A skin lesion imaged with a dermatoscope.
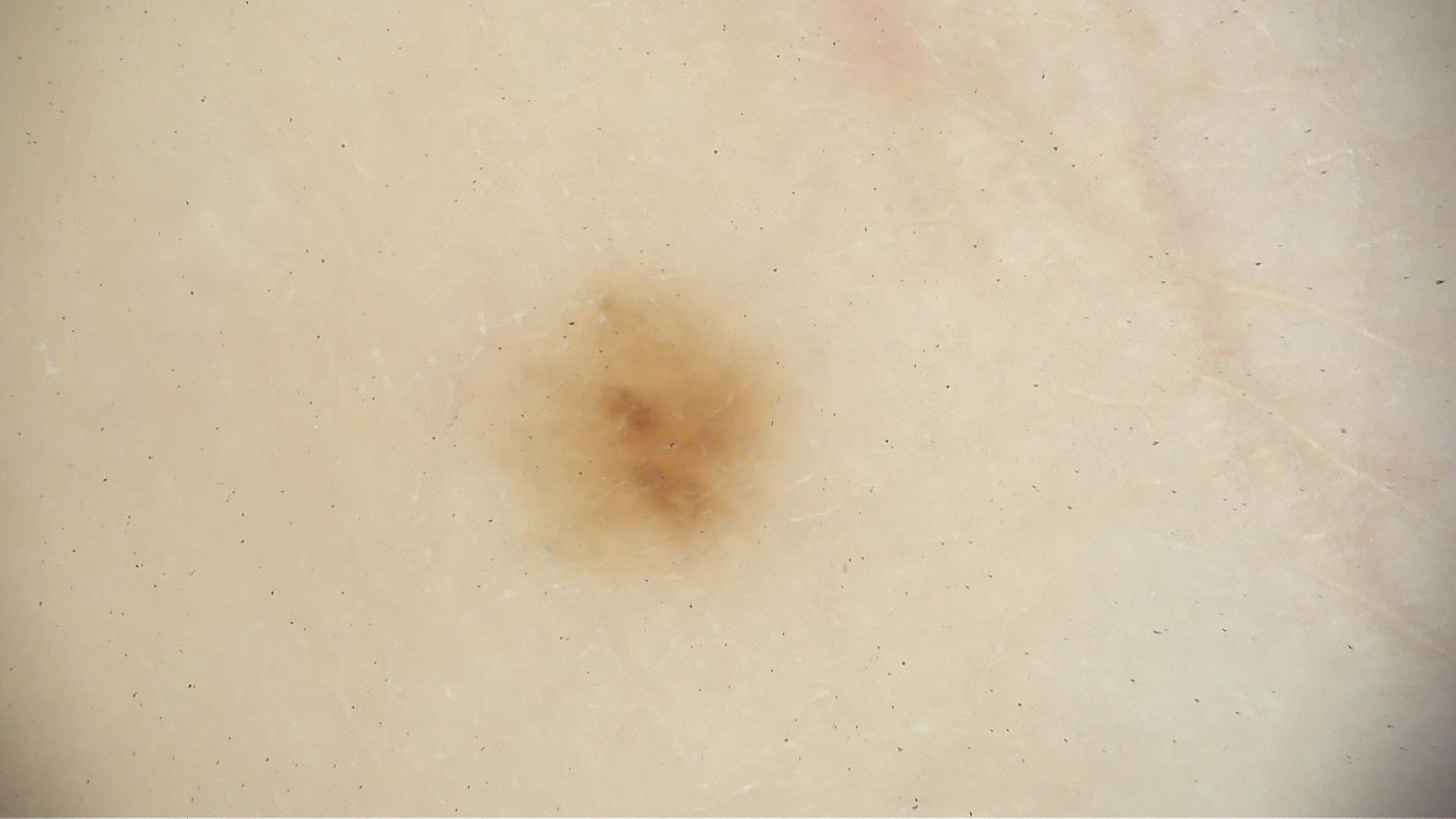Impression:
The diagnosis was a benign lesion — a dysplastic junctional nevus.